Dermoscopy of a skin lesion:
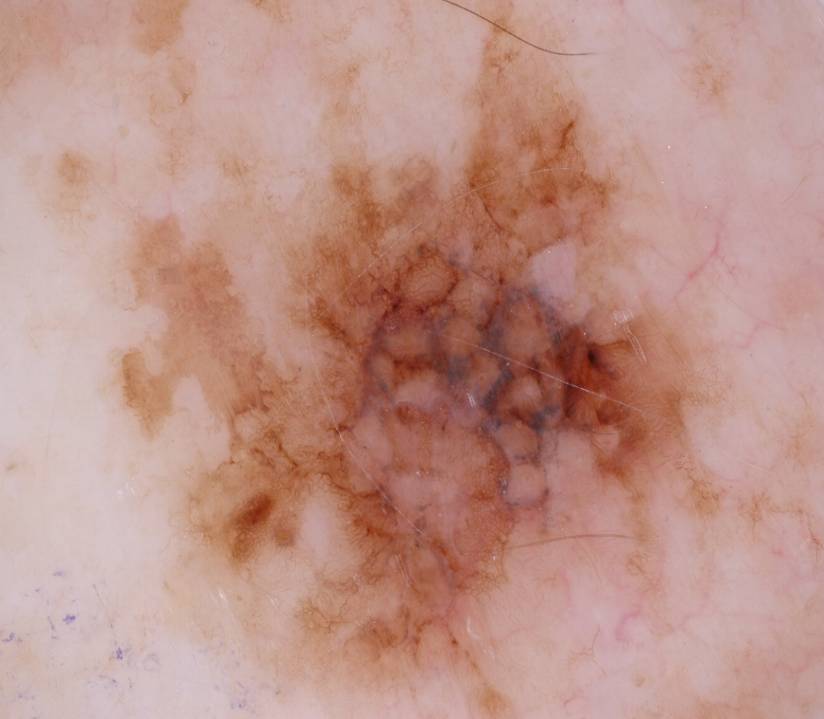lesion location = <bbox>118, 1, 718, 682</bbox> | features = pigment network; absent: negative network, milia-like cysts, globules, and streaks | impression = a melanoma, a skin cancer.